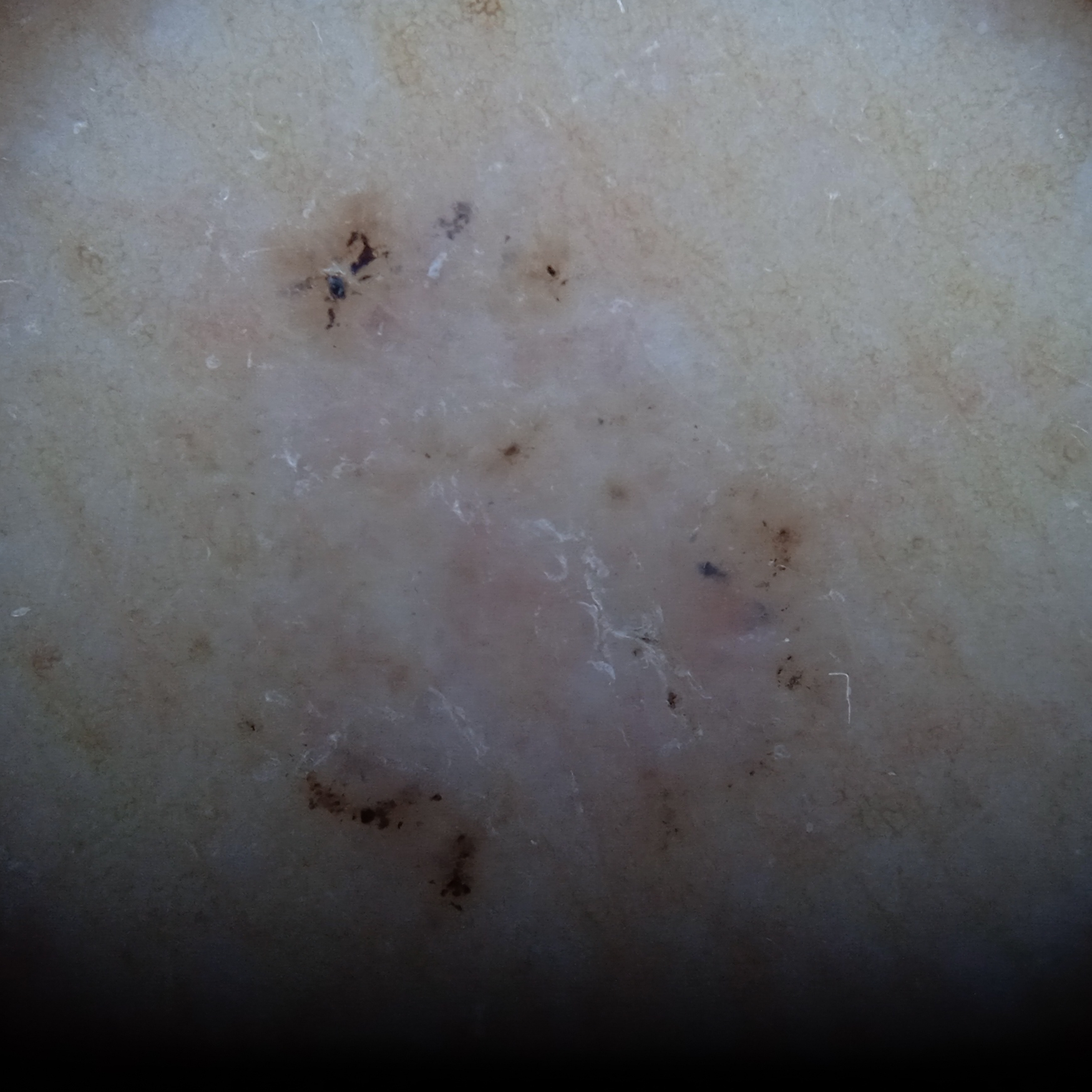  patient:
    age: 60
    sex: female
  referral: clinical suspicion of basal cell carcinoma
  sun_reaction: skin tans without first burning
  image: dermoscopy
  mole_burden: few melanocytic nevi overall
  risk_factors:
    positive:
      - a personal history of skin cancer
      - a personal history of cancer
    negative:
      - no immunosuppression
      - no sunbed use
  lesion_size:
    diameter_mm: 7.8
  diagnosis:
    name: basal cell carcinoma
    malignancy: malignant